This image was taken at an angle; the affected area is the leg: 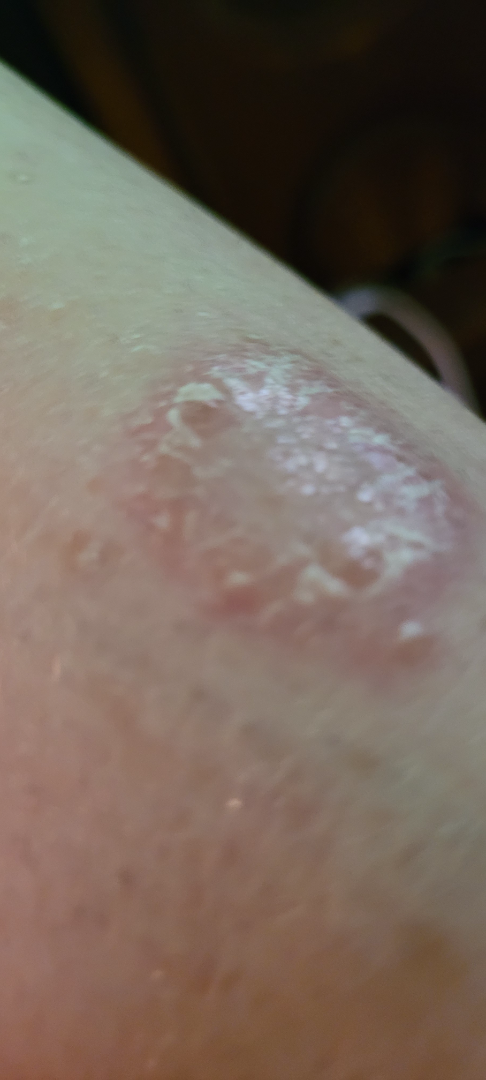Assessment: Diagnostic features were not clearly distinguishable in this photograph.